A dermoscopic image of a skin lesion, a male subject.
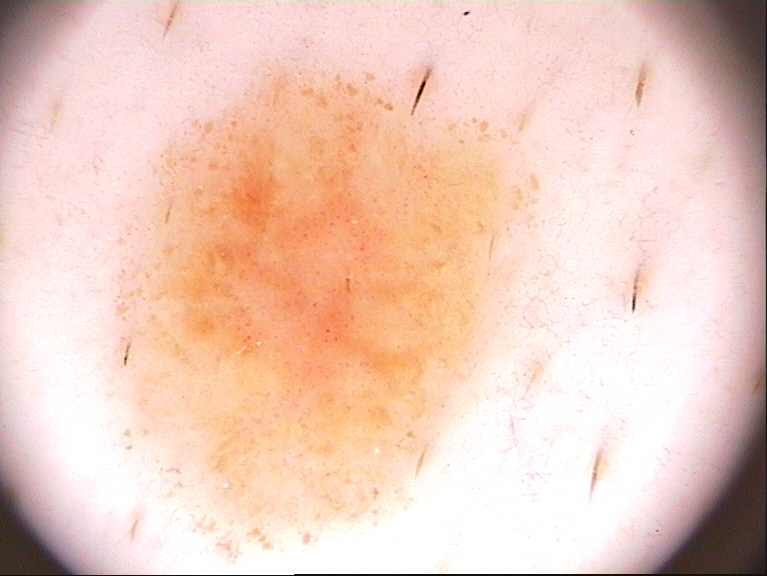Dermoscopic assessment notes globules, with no negative network, milia-like cysts, pigment network, or streaks. With coordinates (x1, y1, x2, y2), the lesion is located at [102, 50, 541, 567]. Diagnosed as a melanocytic nevus.